A dermatoscopic image of a skin lesion.
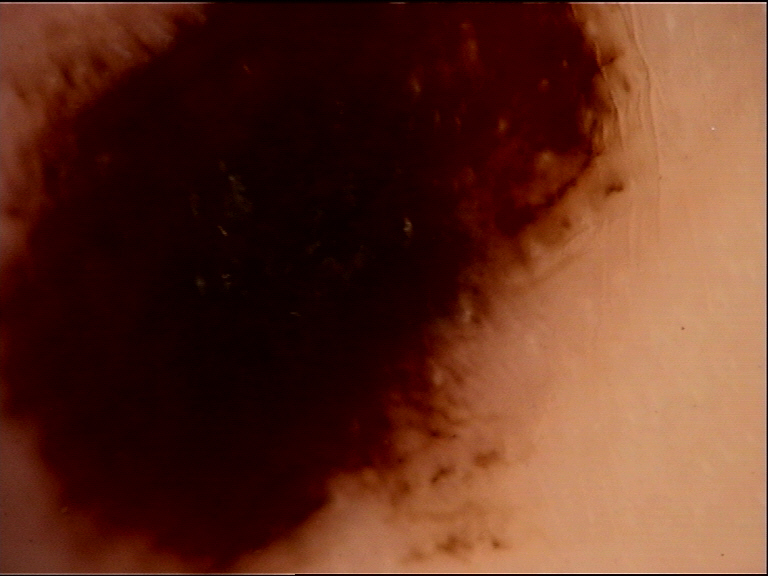Conclusion:
Classified as a benign lesion — an acral dysplastic junctional nevus.